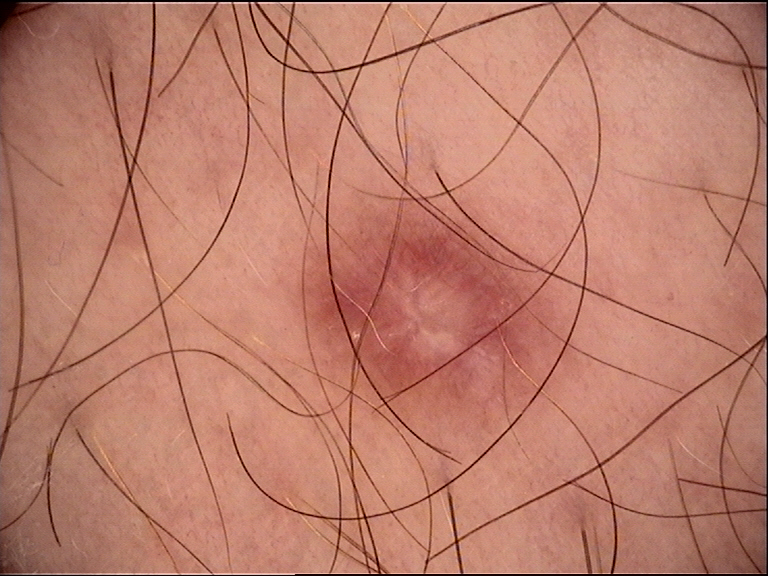Q: What was the diagnostic impression?
A: dermatofibroma (expert consensus)